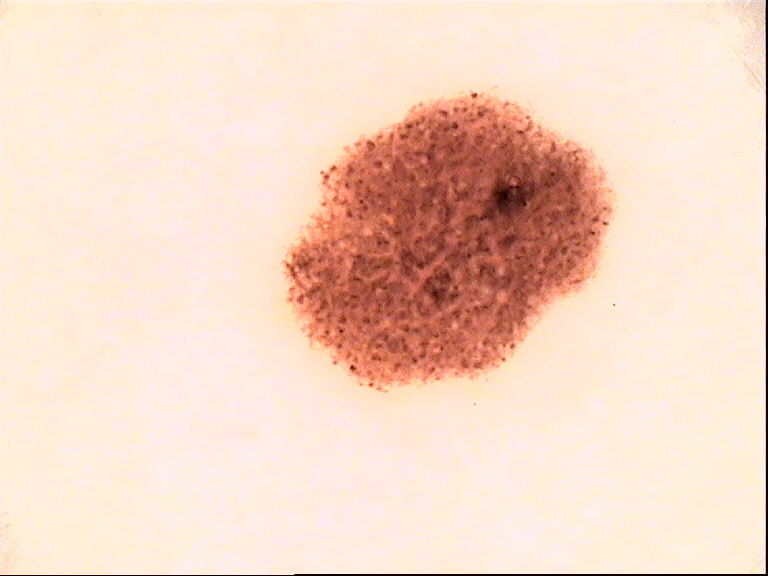Case:
– image type — dermatoscopy
– assessment — dysplastic junctional nevus (expert consensus)